The photograph is a close-up of the affected area · the lesion is described as rough or flaky · reported duration is about one day · the patient is male · skin tone: Fitzpatrick phototype II; lay reviewers estimated MST 3 (US pool) or 2 (India pool) · no relevant systemic symptoms · the affected area is the leg — 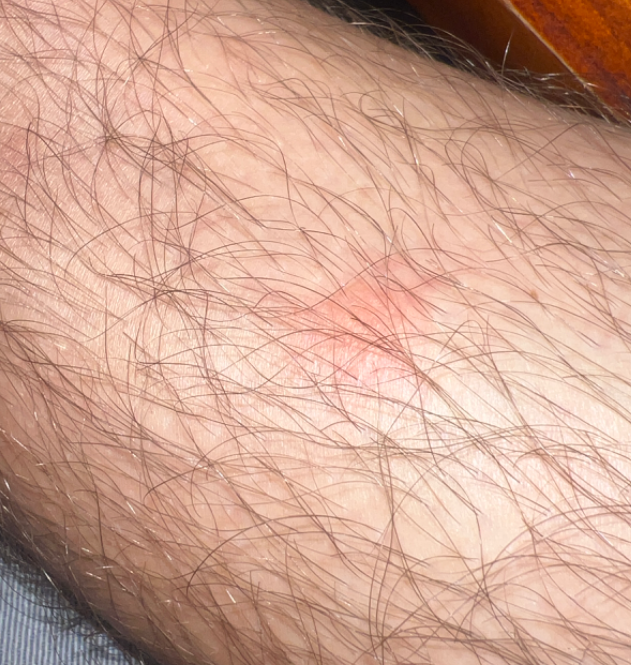Q: What is the differential diagnosis?
A: Contact dermatitis (1.00)